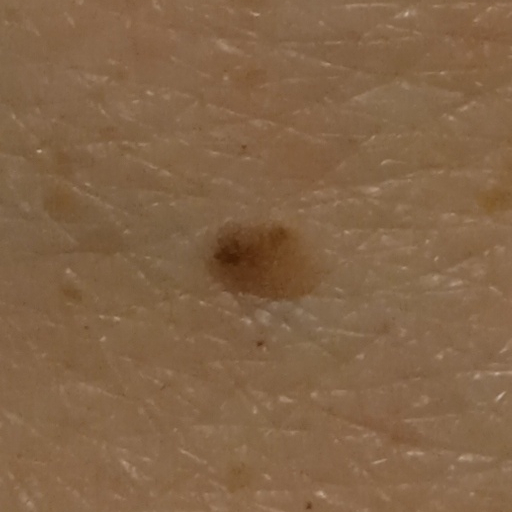{"referral": "research study (no referral diagnosis)", "sun_reaction": "skin tans without first burning", "risk_factors": {"positive": ["a personal history of cancer"]}, "patient": {"age": 84, "sex": "female"}, "diagnosis": {"name": "seborrheic keratosis", "malignancy": "benign"}}